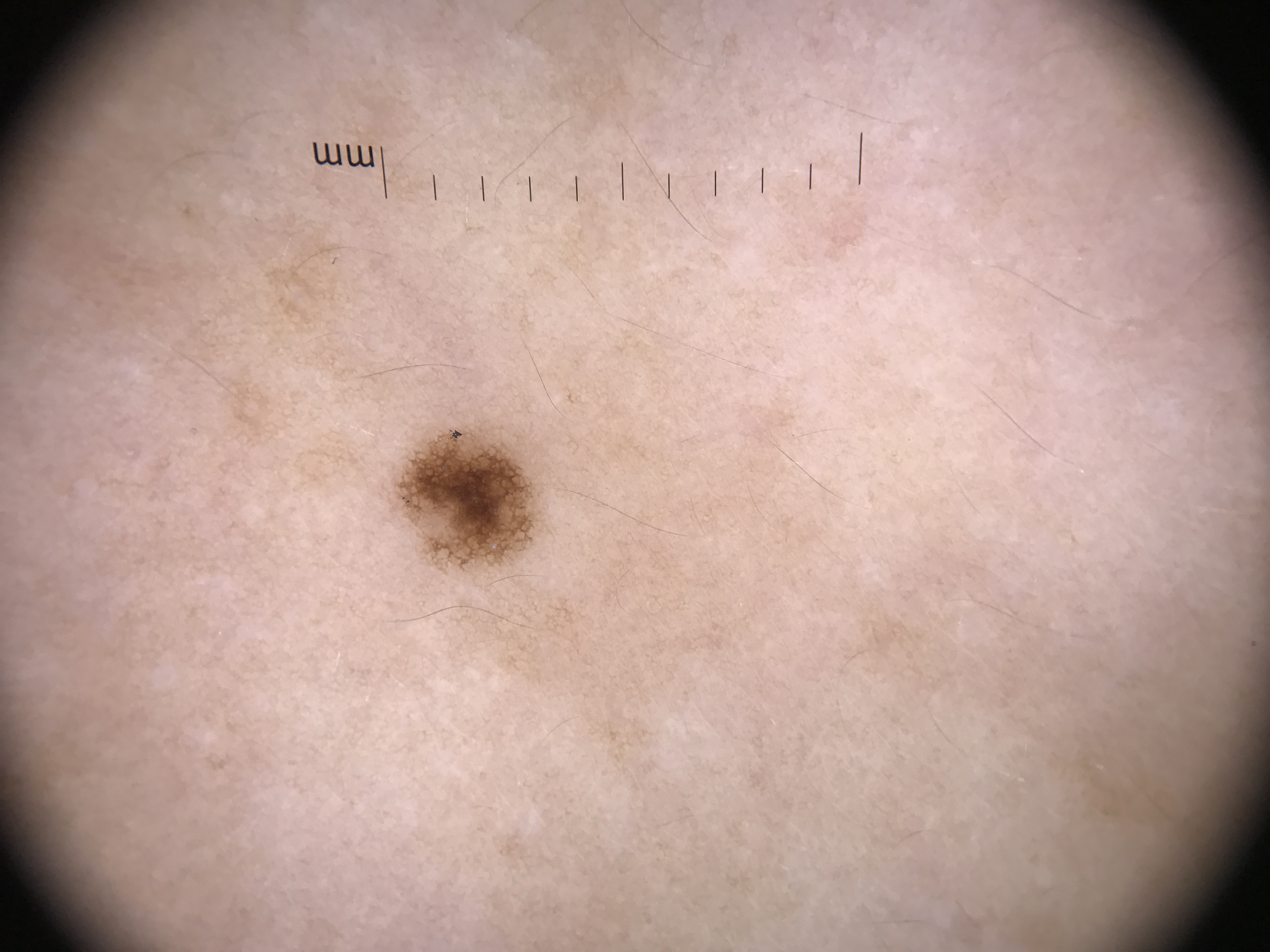category — banal; assessment — junctional nevus (expert consensus).